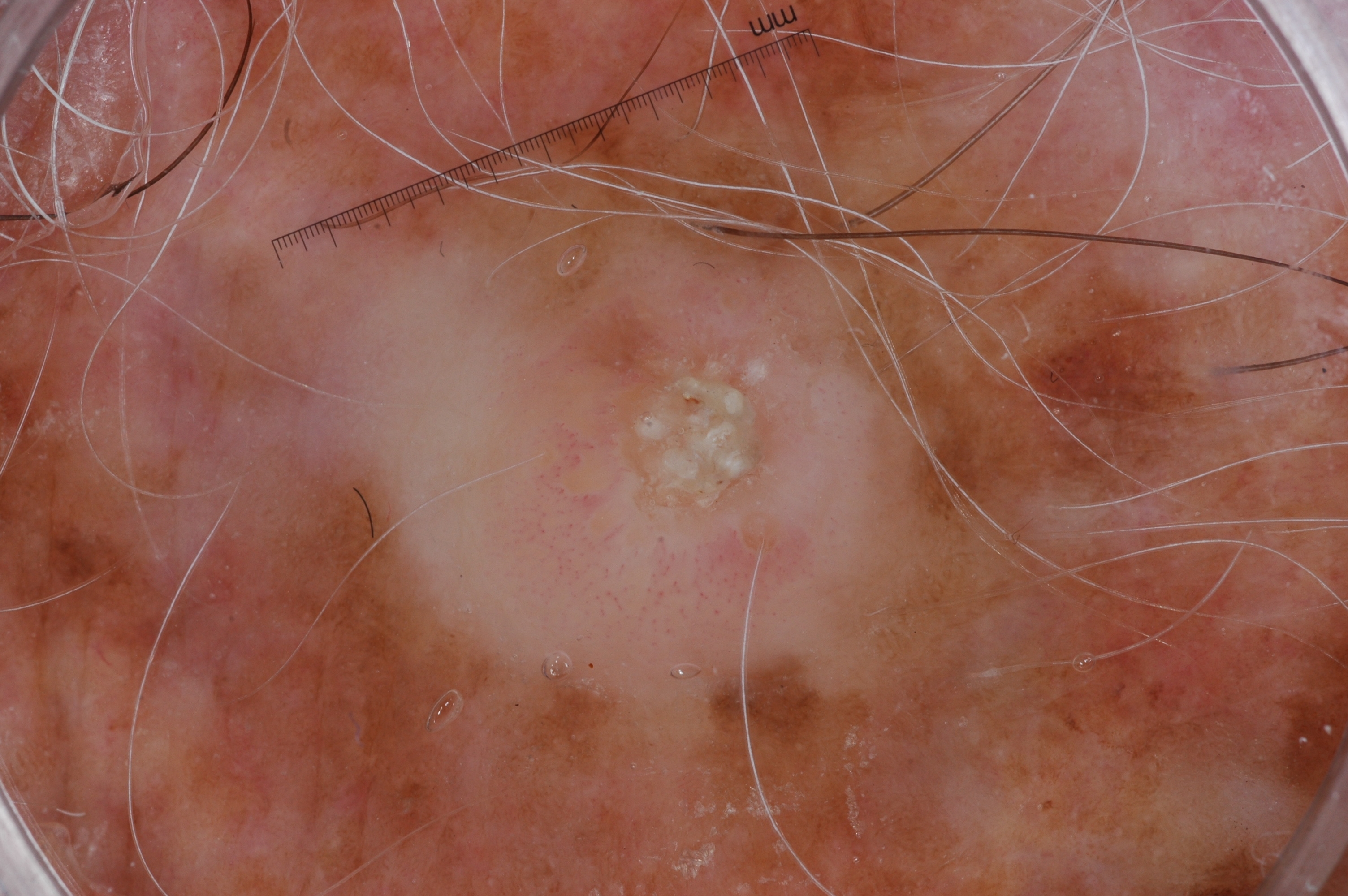A male subject, aged 63 to 67. Dermoscopy of a skin lesion. The visible lesion spans left=108, top=93, right=998, bottom=772. Dermoscopic review identifies milia-like cysts; no streaks, negative network, or pigment network. The lesion occupies roughly 39% of the field. The diagnostic assessment was a seborrheic keratosis, a benign lesion.